A dermoscopic image of a skin lesion.
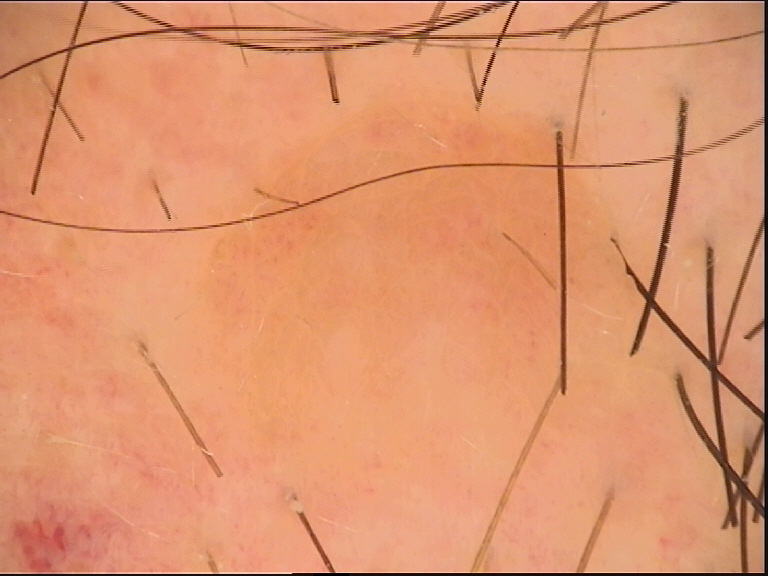category: banal
assessment: junctional nevus (expert consensus)